A dermoscopic close-up of a skin lesion.
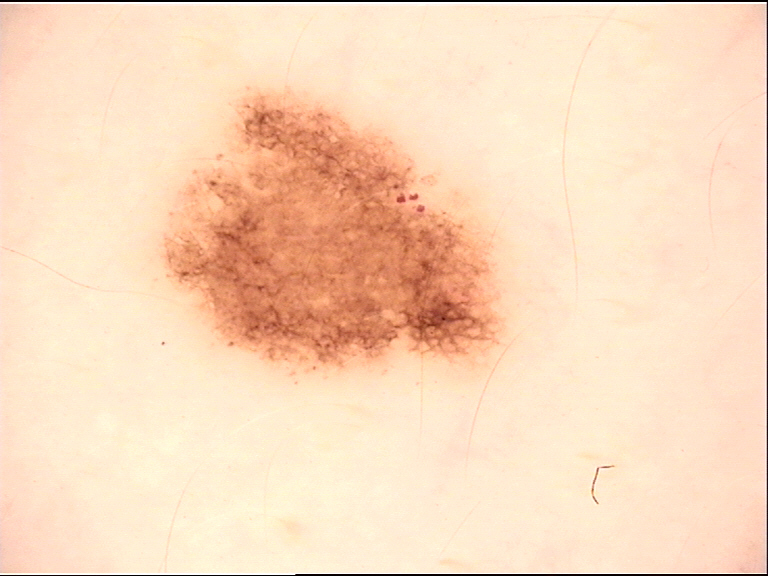diagnostic label = dysplastic junctional nevus (expert consensus).